The patient reports a history of sunbed use · a female subject 47 years old · the patient says their skin tans without first burning · imaged for a research study, with no referral diagnosis recorded · a dermatoscopic image of a skin lesion · the patient describes having a moderate number of moles.
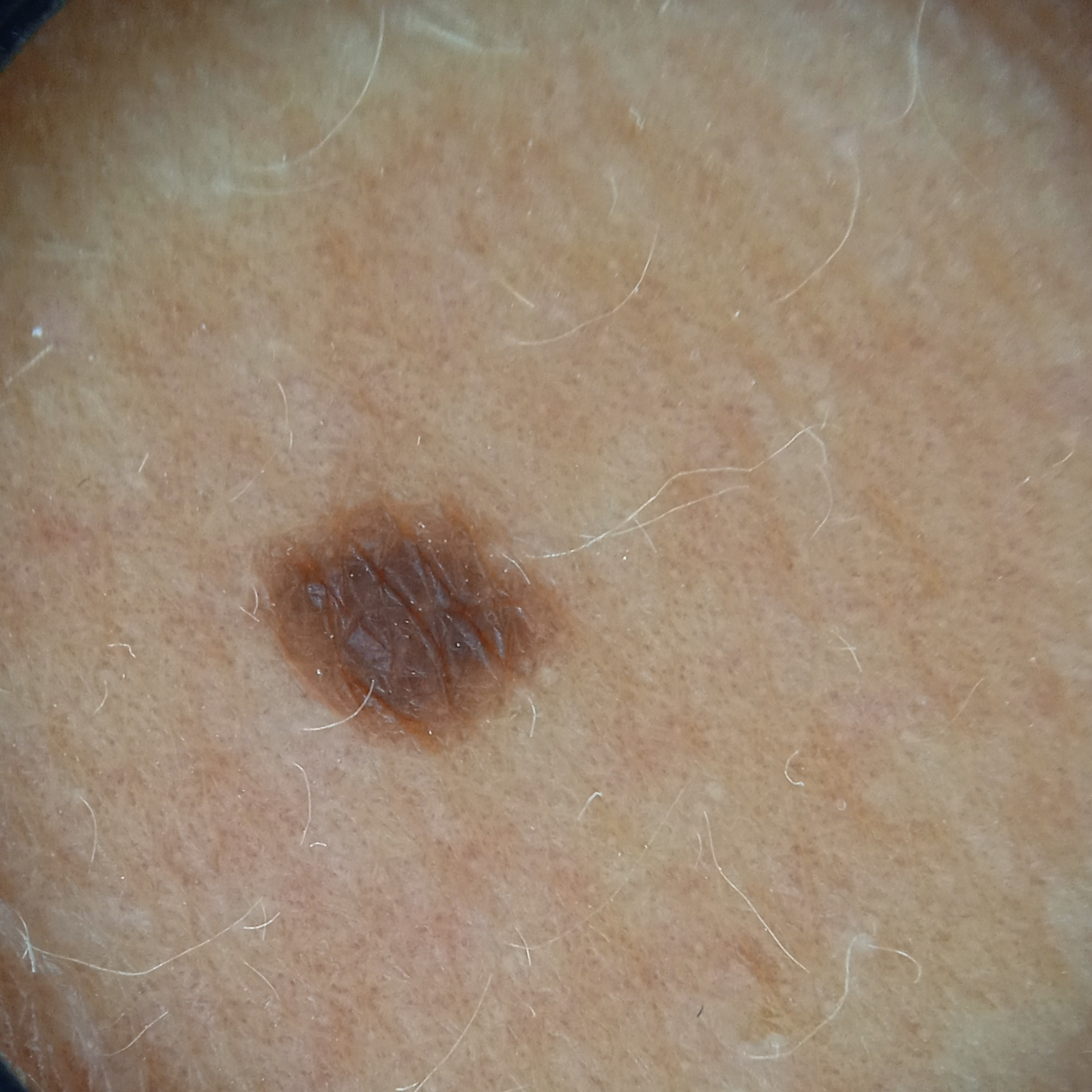Located on an arm. The lesion measures approximately 3.3 mm. On independent review by four dermatologists, the agreed diagnosis was a melanocytic nevus.